FST III; lay reviewers estimated a MST of 2. The patient reports itching. The condition has been present for less than one week. Self-categorized by the patient as a rash. The affected area is the arm, leg and back of the hand. This image was taken at an angle. The patient reports the lesion is raised or bumpy:
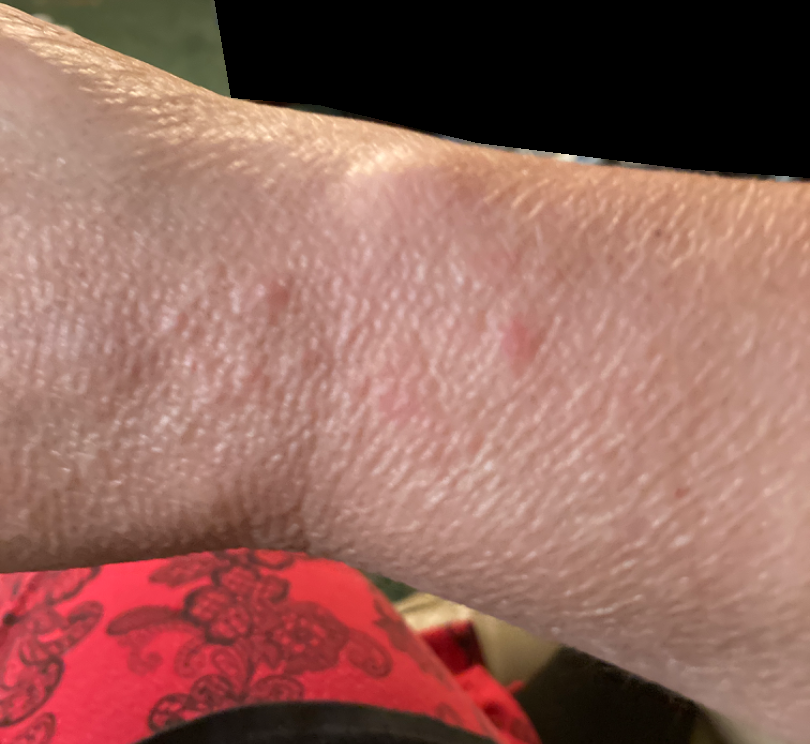Findings: The reviewing dermatologist's impression was: Eczema (primary); Allergic Contact Dermatitis (possible).